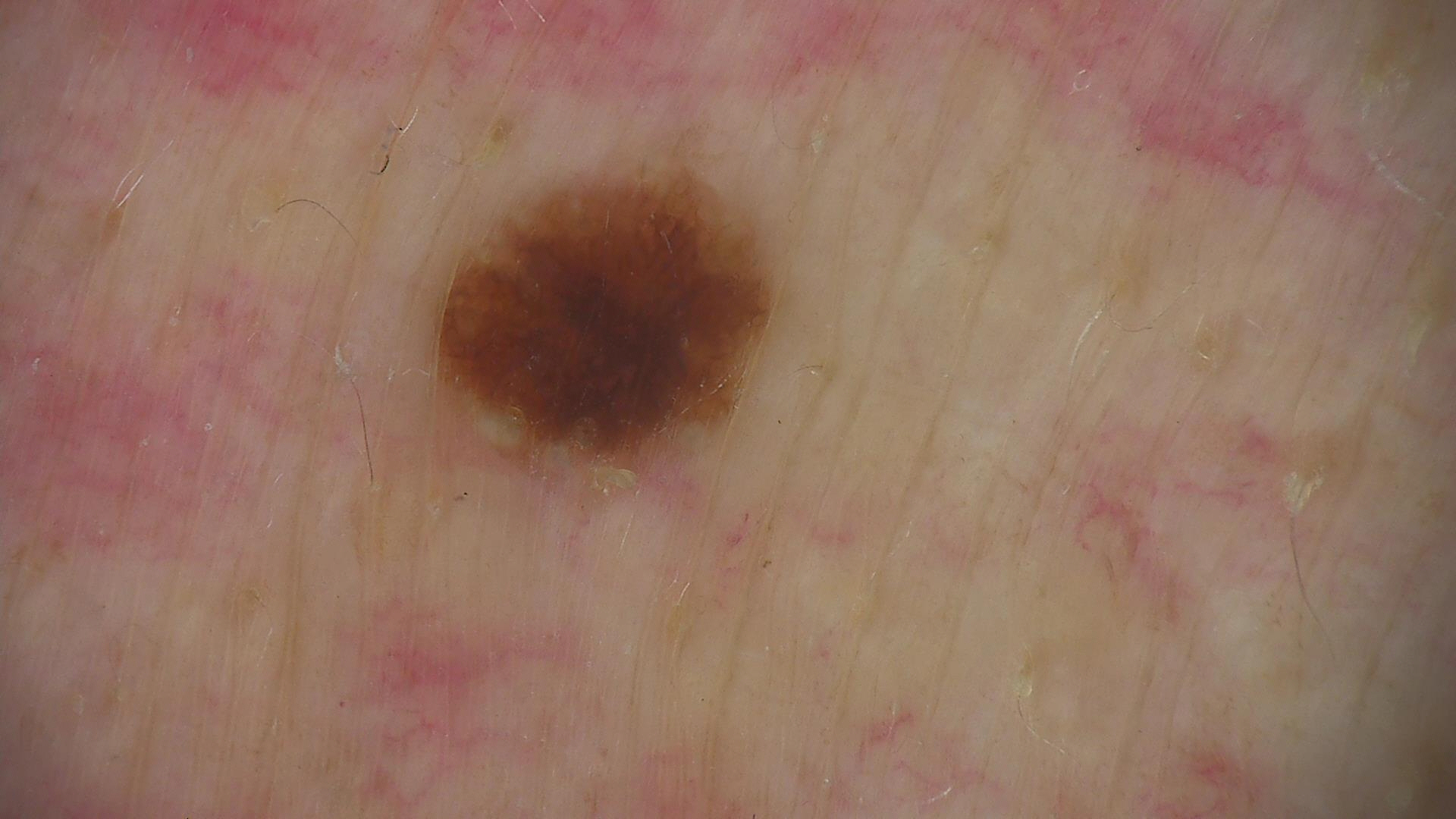A dermoscopic image of a skin lesion.
Diagnosed as a dysplastic junctional nevus.